Located on the arm, the subject is female, the photograph is a close-up of the affected area — 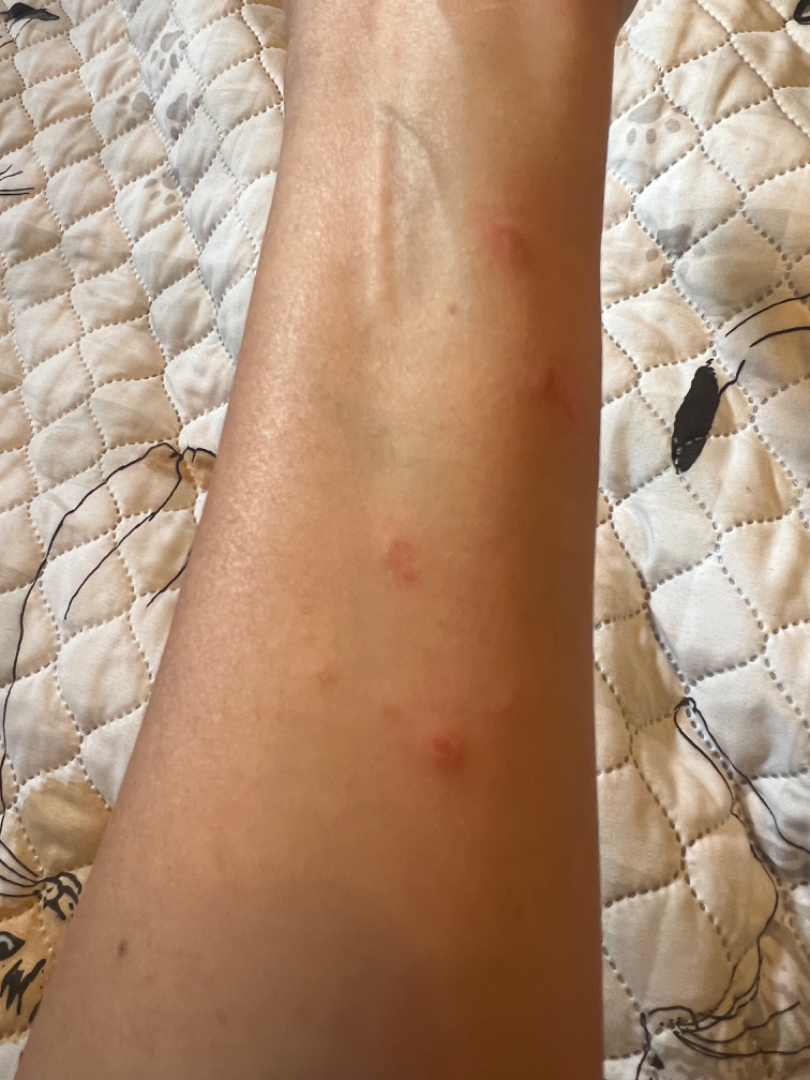History: Texture is reported as raised or bumpy and fluid-filled. The condition has been present for about one day. Skin tone: FST V; lay reviewers estimated MST 3 or 4. Impression: On photographic review by a dermatologist, Herpes Zoster (0.50); Allergic Contact Dermatitis (0.50).